This is a close-up image; male subject, age 40–49; the leg is involved — 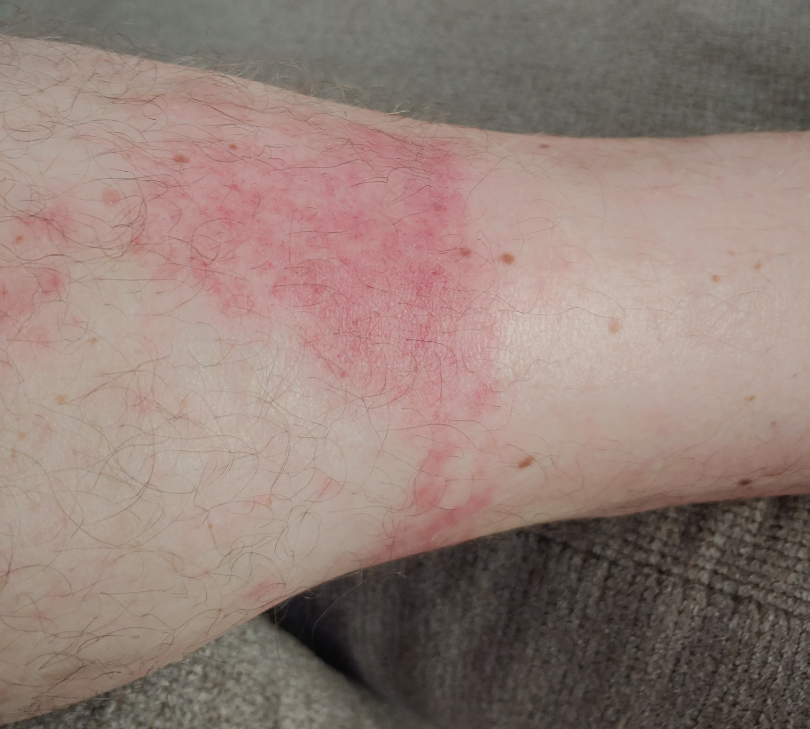Q: What is the dermatologist's impression?
A: Allergic Contact Dermatitis (0.67); Irritant Contact Dermatitis (0.33)